Reported duration is one to three months. The lesion involves the arm and back of the hand. The contributor is a female aged 60–69. The patient notes associated fatigue. The patient notes itching, bleeding and bothersome appearance. The patient considered this a rash. A close-up photograph — 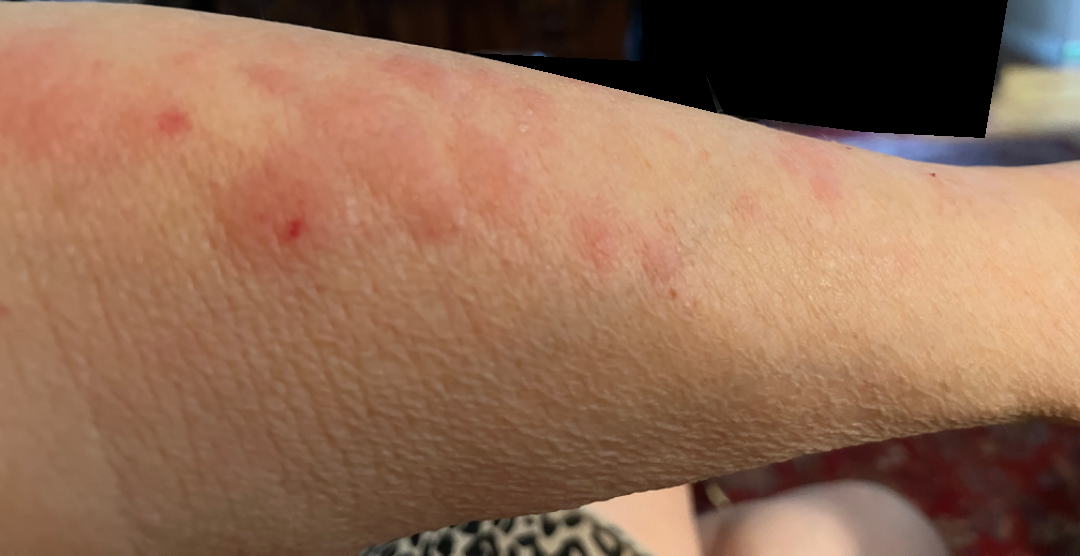Assessment: On dermatologist assessment of the image: most consistent with Acute dermatitis, NOS.